A dermoscopy image of a single skin lesion.
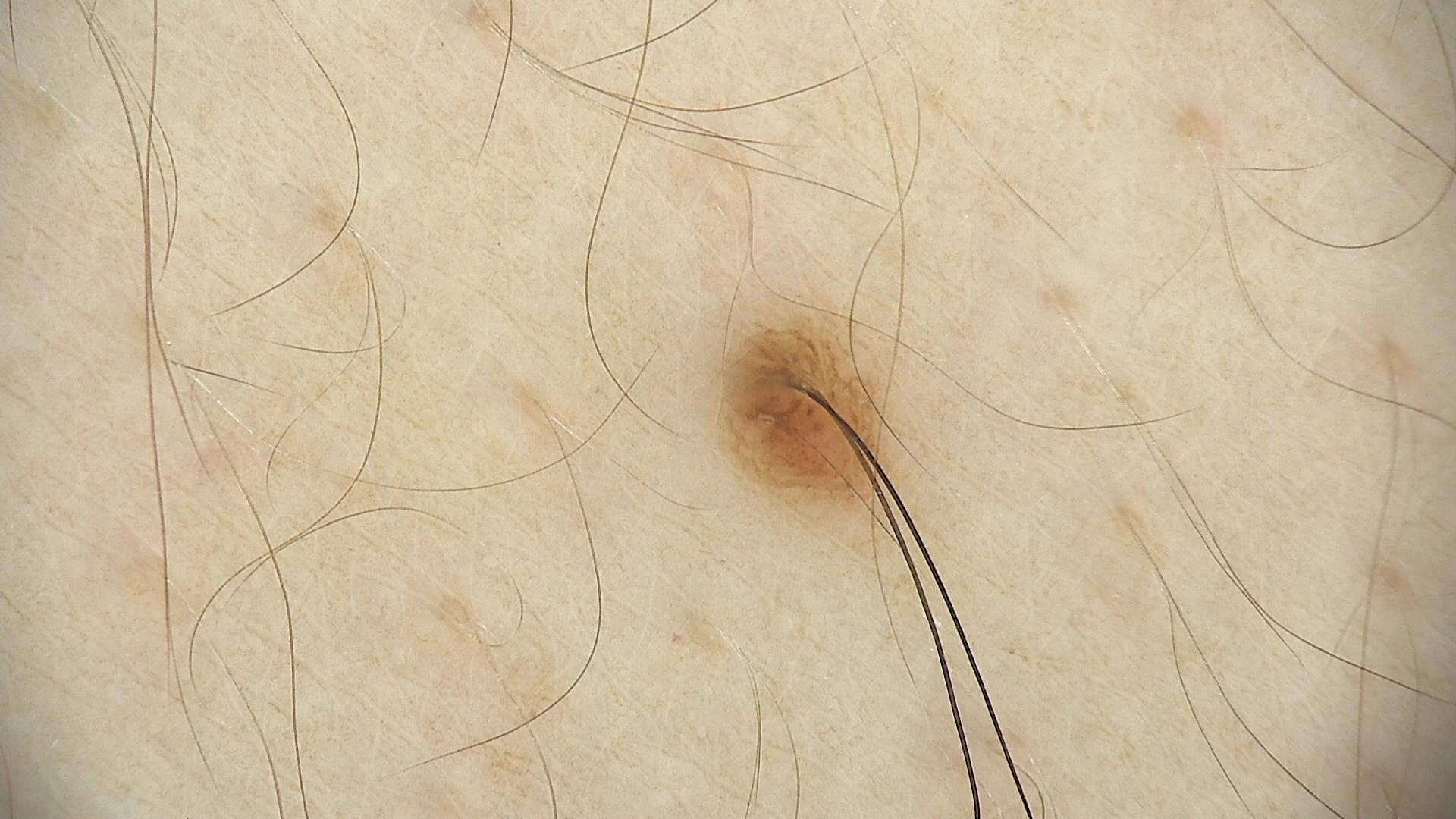Classified as a junctional nevus.